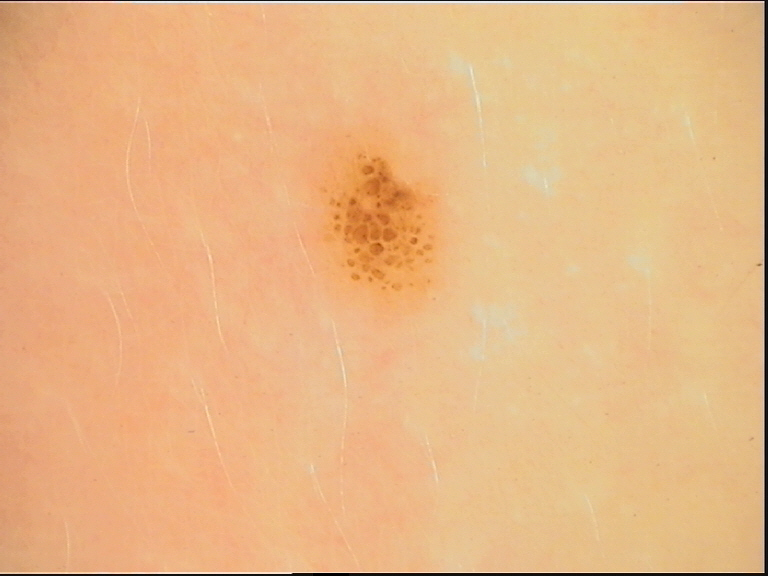image type = dermatoscopy | assessment = dysplastic junctional nevus (expert consensus).